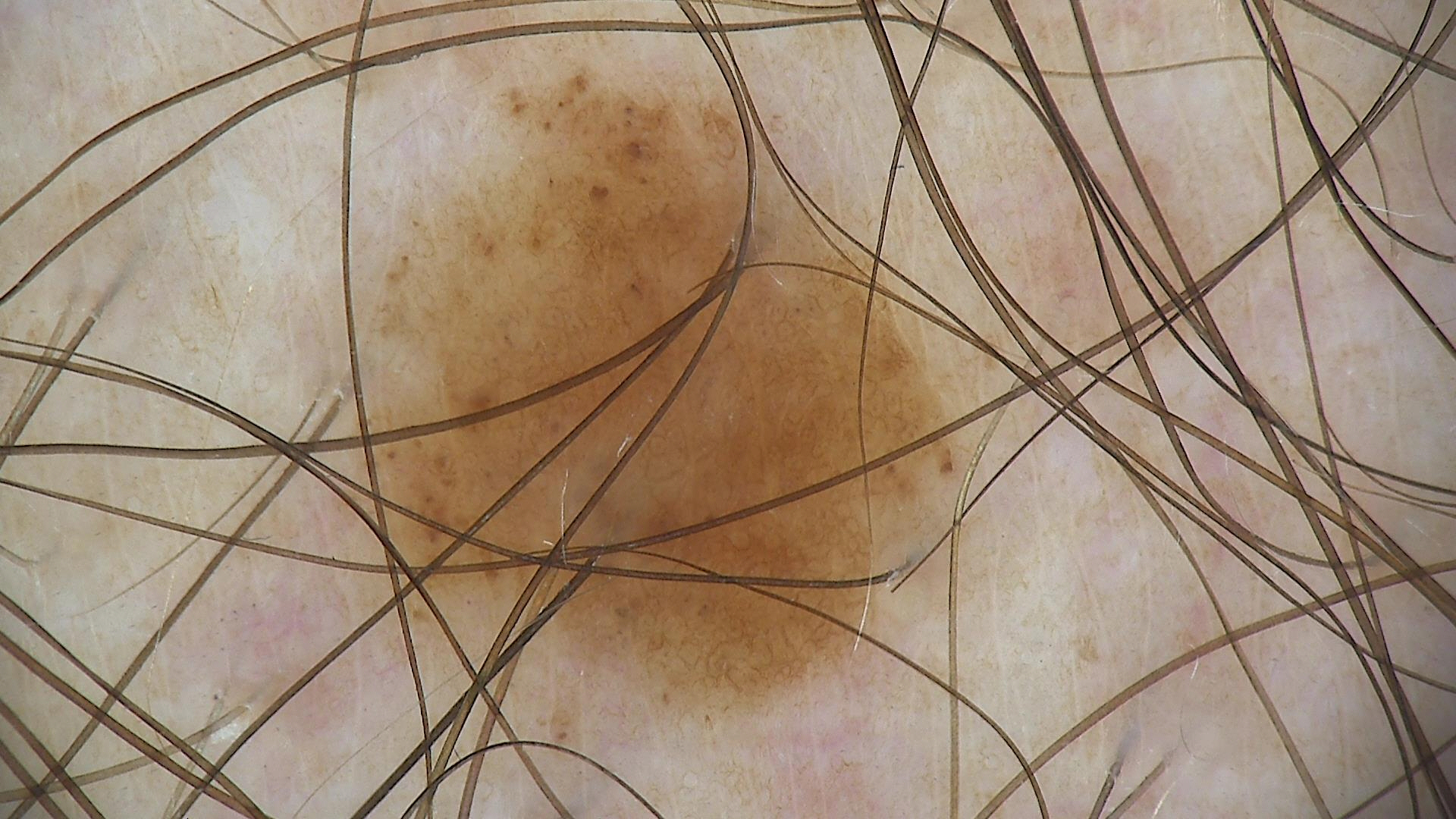<lesion>
  <diagnosis>
    <name>dysplastic junctional nevus</name>
    <code>jd</code>
    <malignancy>benign</malignancy>
    <super_class>melanocytic</super_class>
    <confirmation>expert consensus</confirmation>
  </diagnosis>
</lesion>